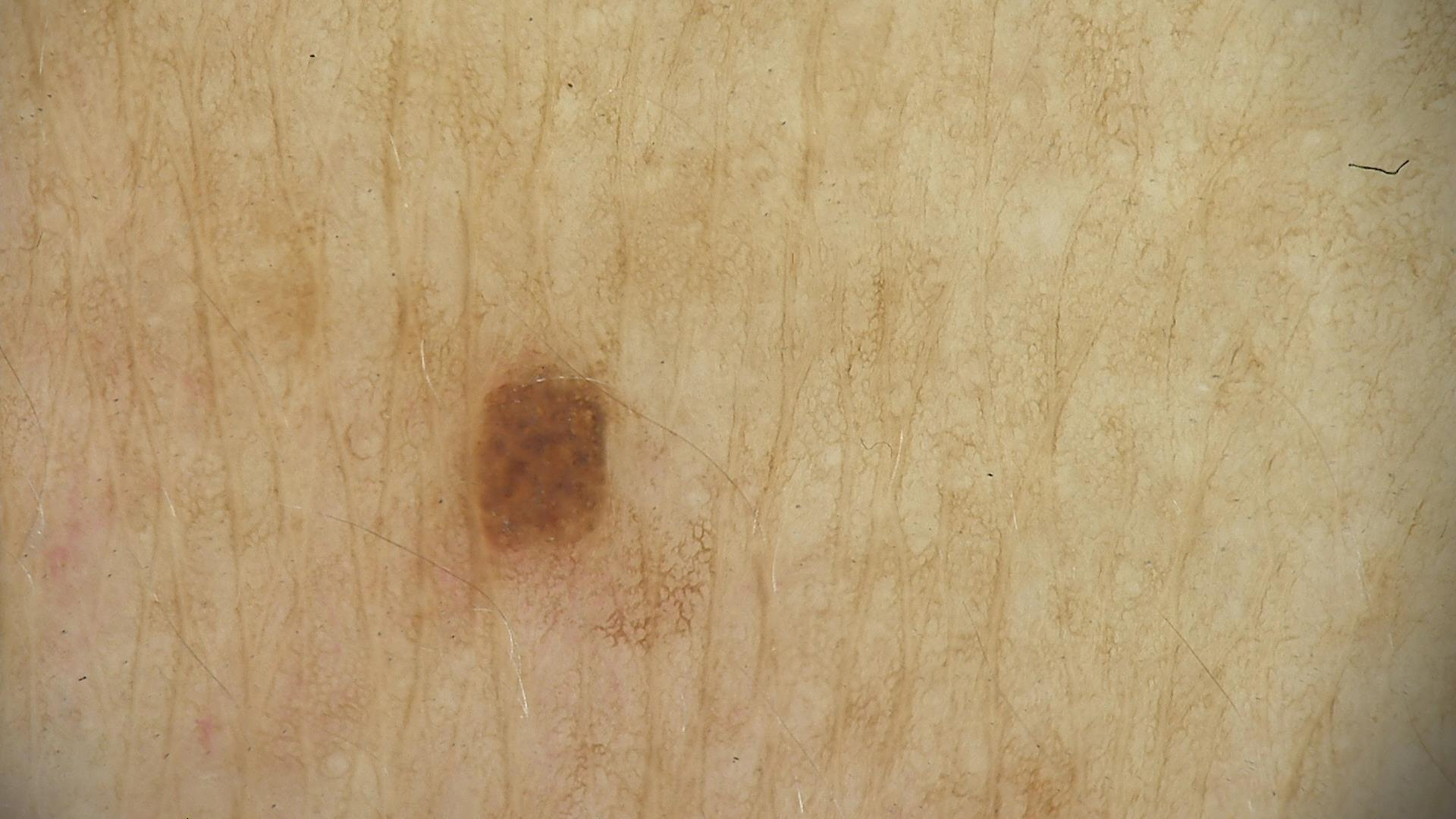Summary: A dermoscopic photograph of a skin lesion. Conclusion: The diagnostic label was a dysplastic junctional nevus.